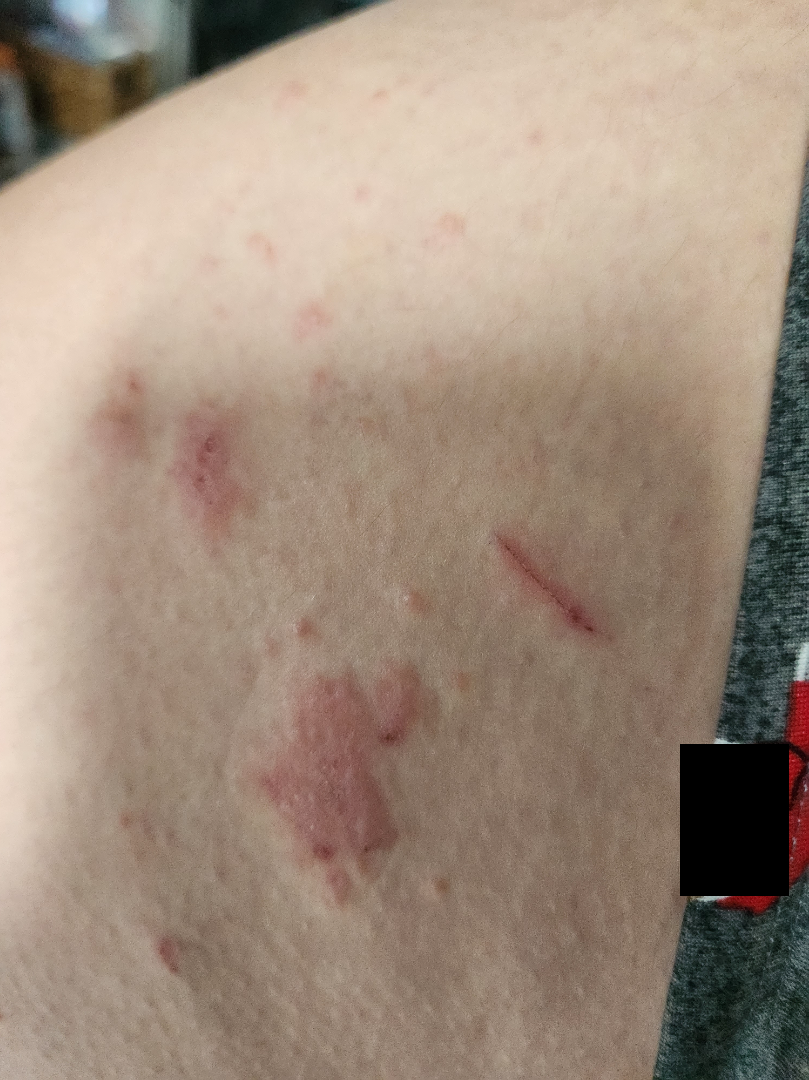<report>
<body_site>leg</body_site>
<shot_type>close-up</shot_type>
<differential>
  <Allergic Contact Dermatitis>0.54</Allergic Contact Dermatitis>
  <Eczema>0.23</Eczema>
  <Psoriasis>0.23</Psoriasis>
</differential>
</report>